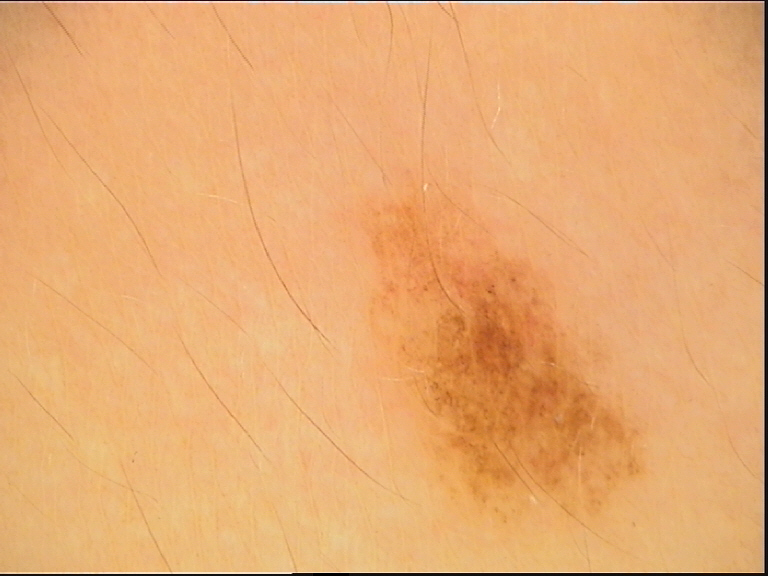Impression:
The diagnosis was a dysplastic junctional nevus.